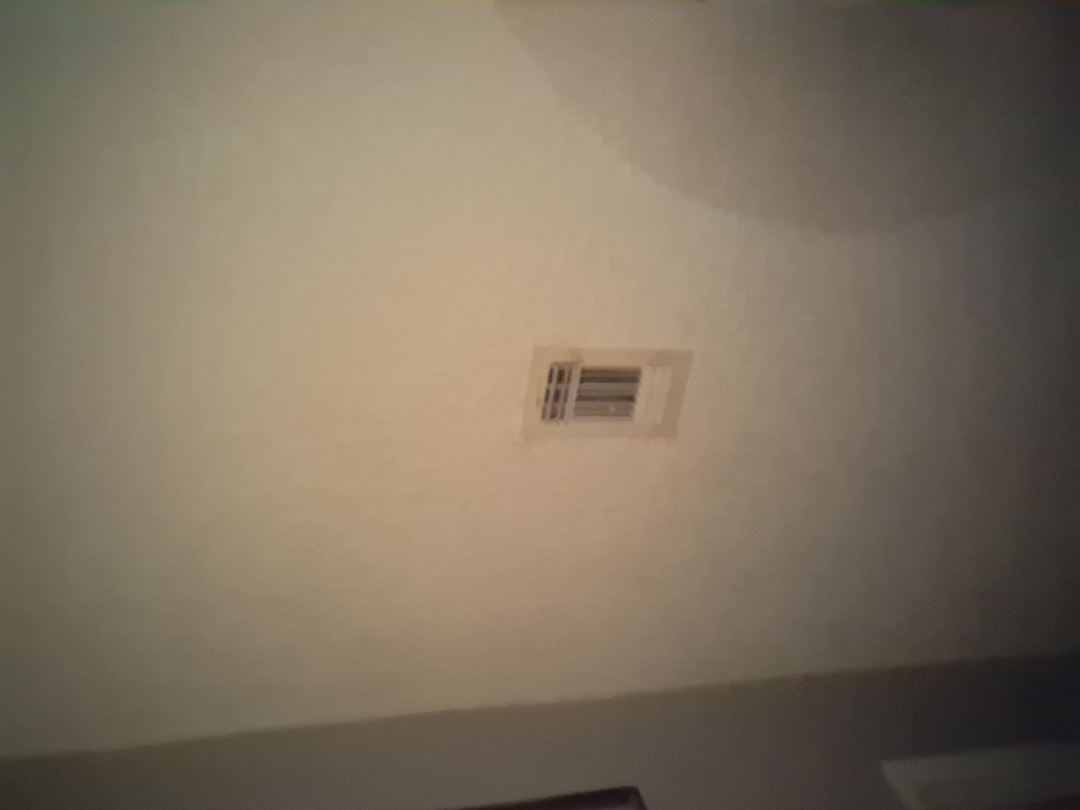The leading consideration is Urticaria.